The photograph was taken at a distance.
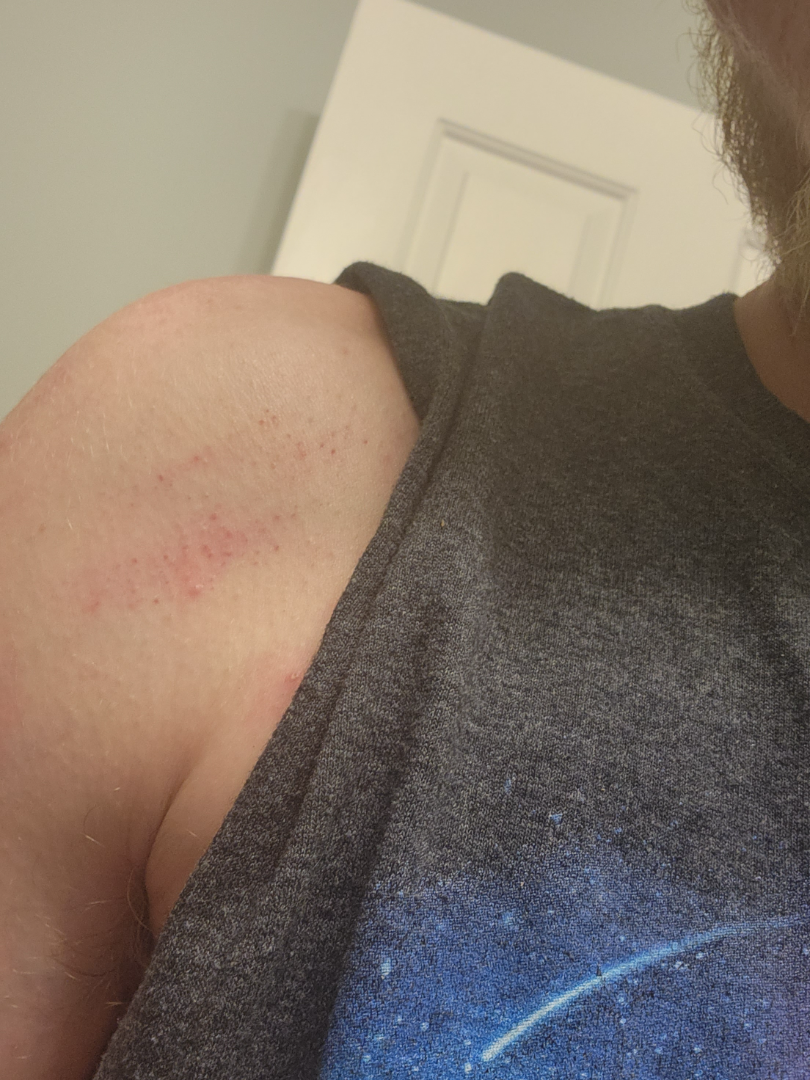History:
Skin tone: lay graders estimated Monk Skin Tone 2–3.
Impression:
One reviewing dermatologist: most consistent with Folliculitis; also raised was Keratosis pilaris; an alternative is Irritant Contact Dermatitis.